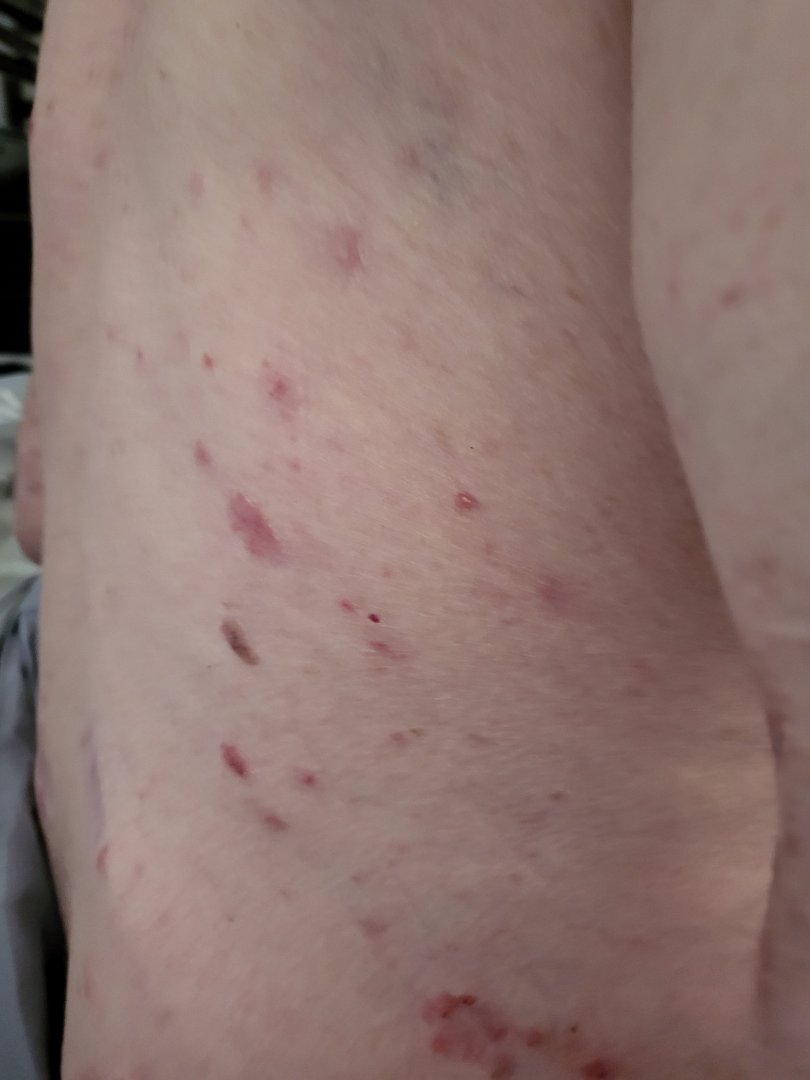Q: What is the affected area?
A: back of the torso
Q: Image view?
A: at an angle
Q: What conditions are considered?
A: Tinea (primary); Impetigo (considered); Folliculitis (considered)